Close-up view · female contributor, age 18–29 · located on the leg · present for less than one week · the contributor notes the lesion is raised or bumpy · Fitzpatrick skin type III; lay reviewers estimated 2 on the Monk skin tone scale · the contributor notes pain and itching · the patient considered this a rash · no associated systemic symptoms reported.
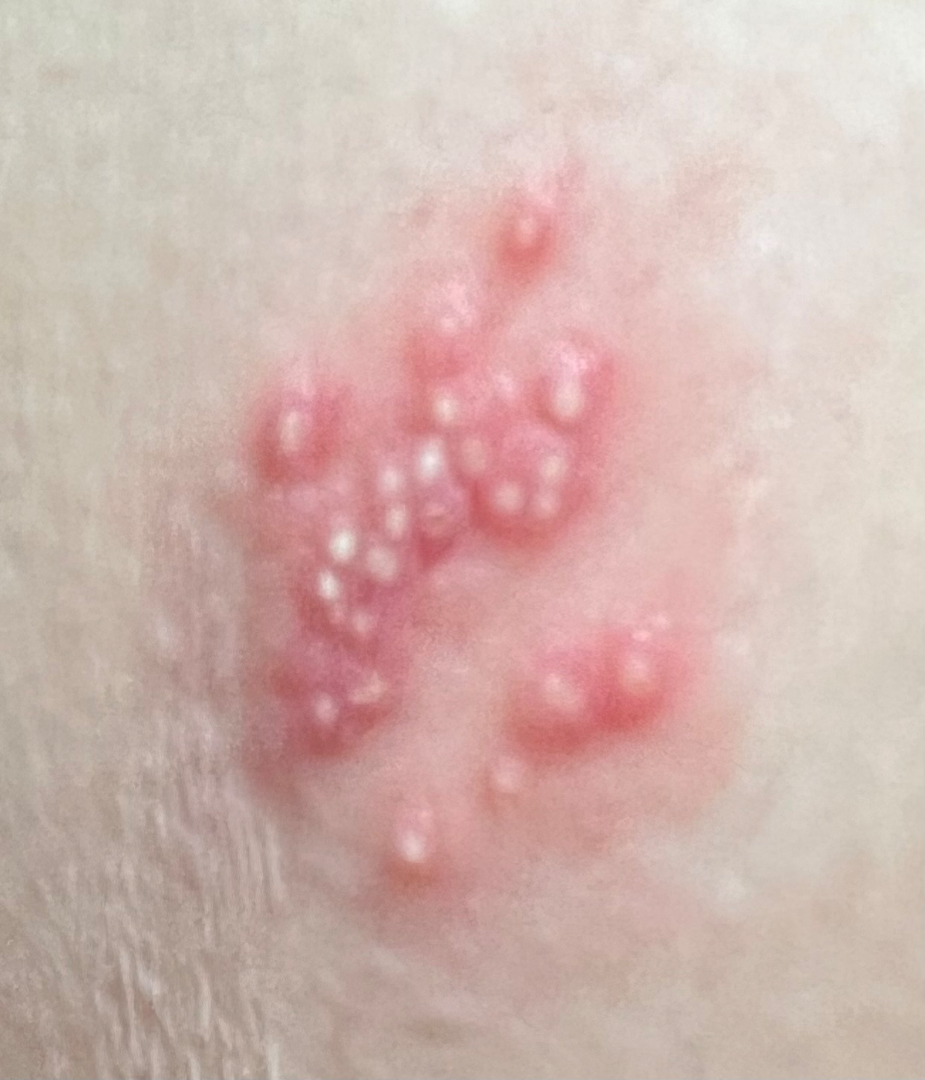On photographic review: in keeping with Herpes Simplex.